A close-up photograph · female patient, age 18–29: 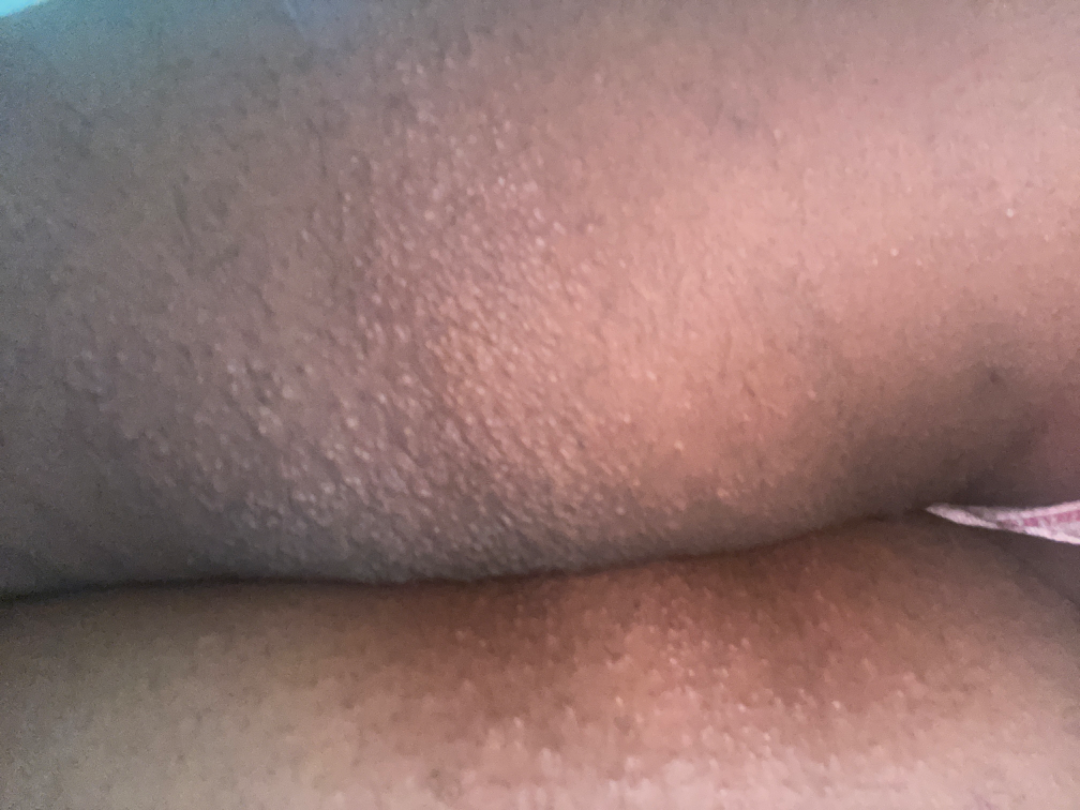impression: the leading consideration is Eczema; possibly Folliculitis.